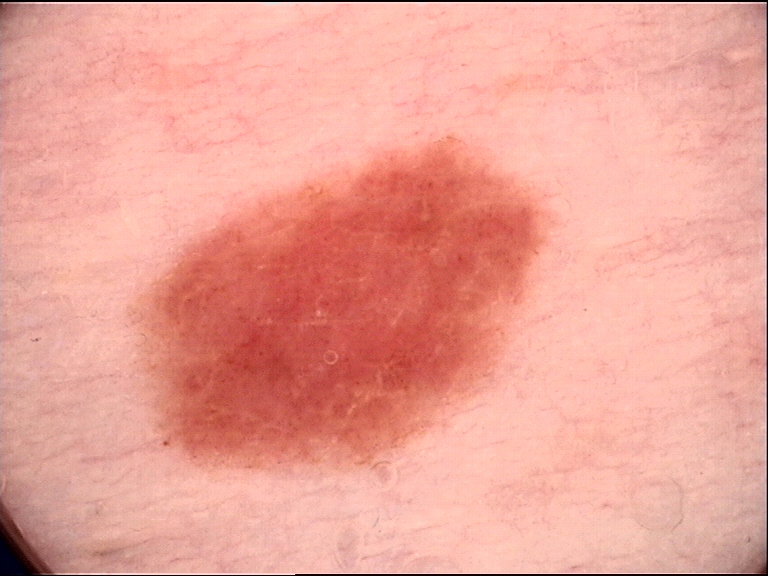Consistent with a banal lesion — a junctional nevus.